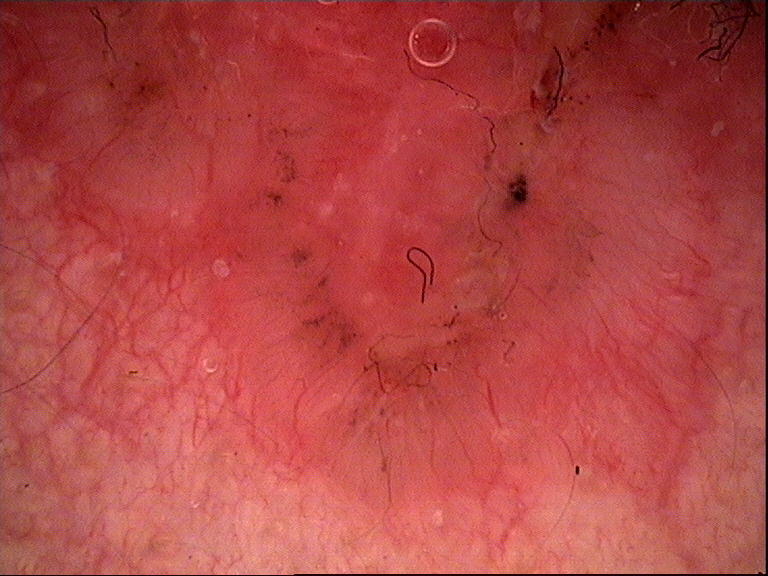A dermoscopic image of a skin lesion. Confirmed on histopathology as a malignant, keratinocytic lesion — a basal cell carcinoma.